A skin lesion imaged with a dermatoscope:
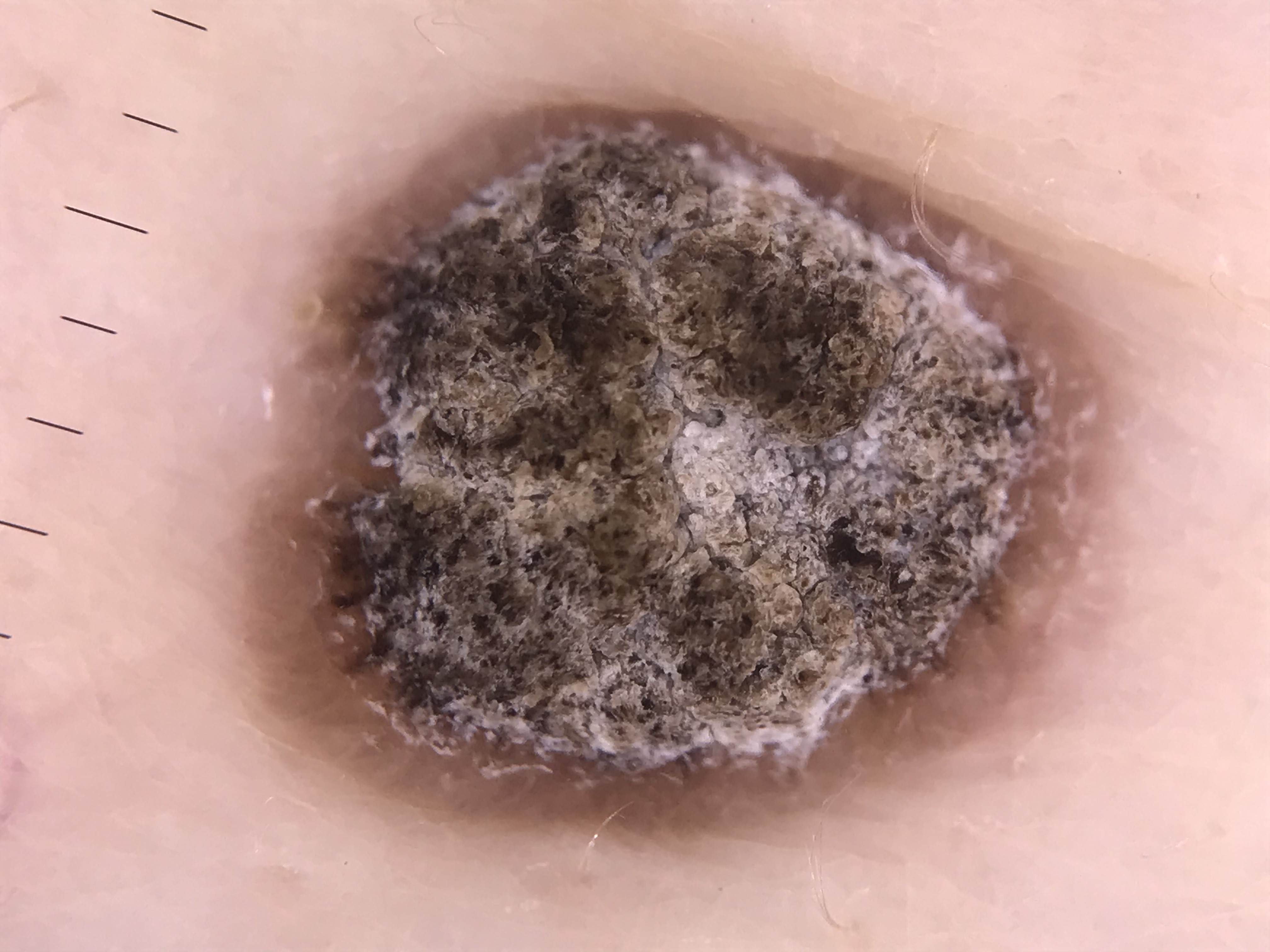<dermoscopy>
  <diagnosis>
    <name>seborrheic keratosis</name>
    <code>sk</code>
    <malignancy>benign</malignancy>
    <super_class>non-melanocytic</super_class>
    <confirmation>expert consensus</confirmation>
  </diagnosis>
</dermoscopy>